A dermoscopic photograph of a skin lesion.
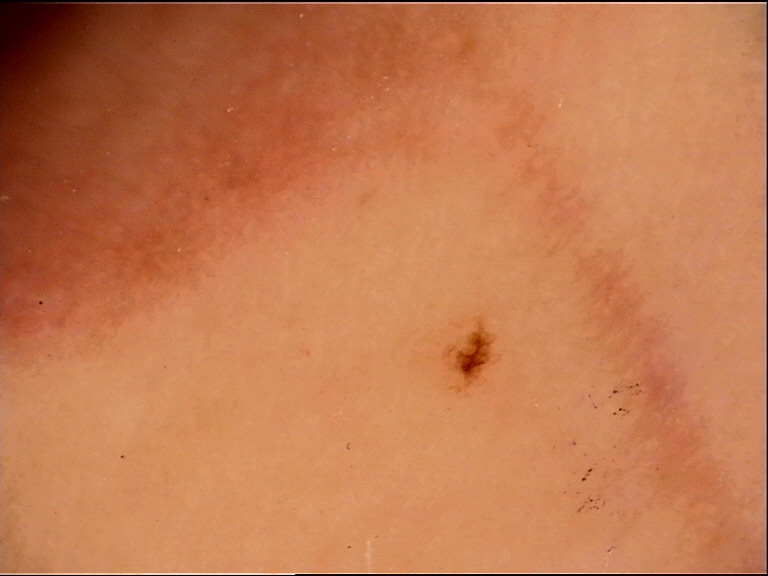Impression:
Labeled as an acral dysplastic junctional nevus.